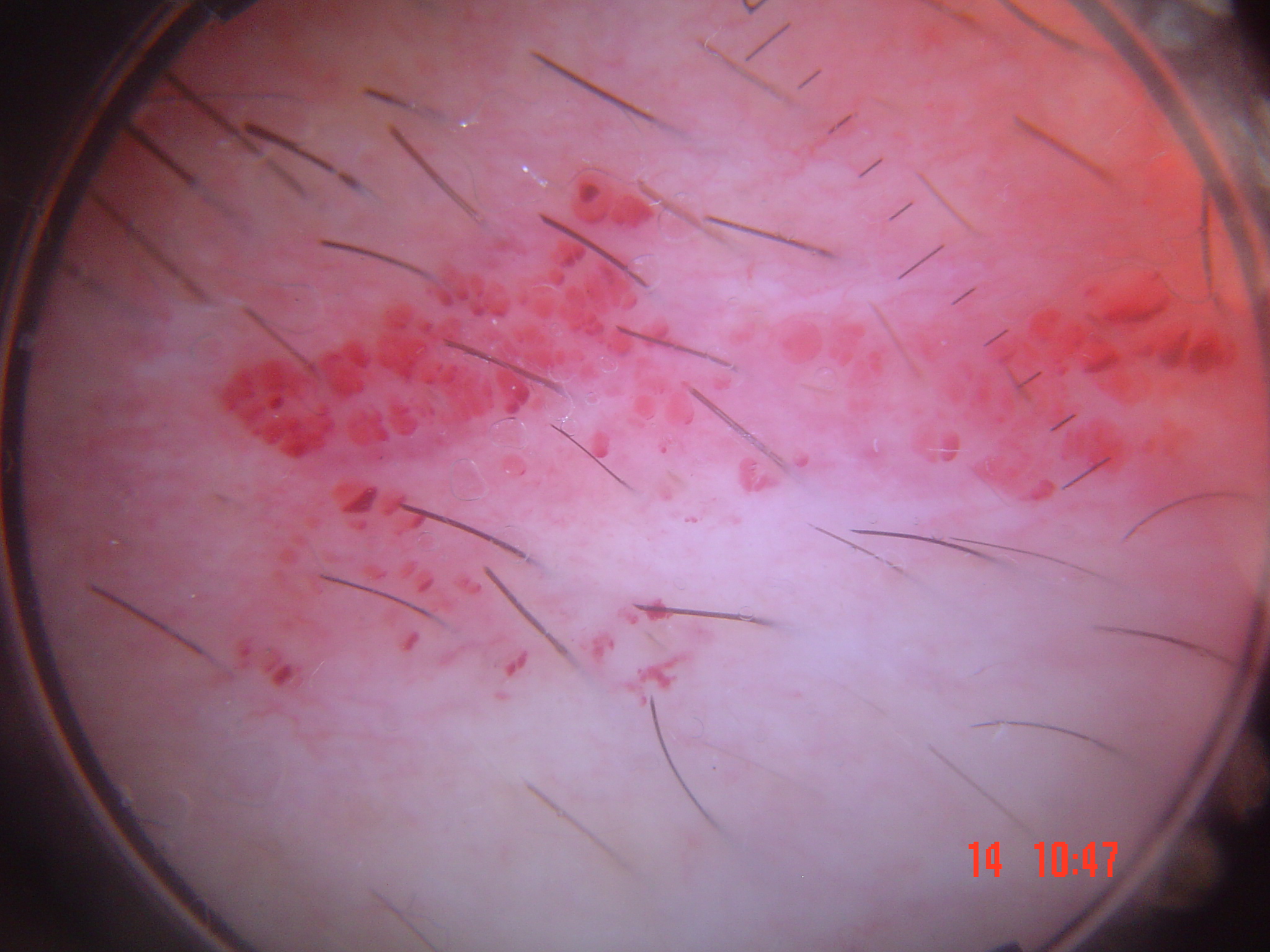modality: dermoscopy; diagnosis: lymphangioma (expert consensus).